The lesion involves the arm and leg. The patient indicates burning, pain and itching. The patient indicates the lesion is raised or bumpy. The patient considered this skin that appeared healthy to them. A close-up photograph. The condition has been present for less than one week.
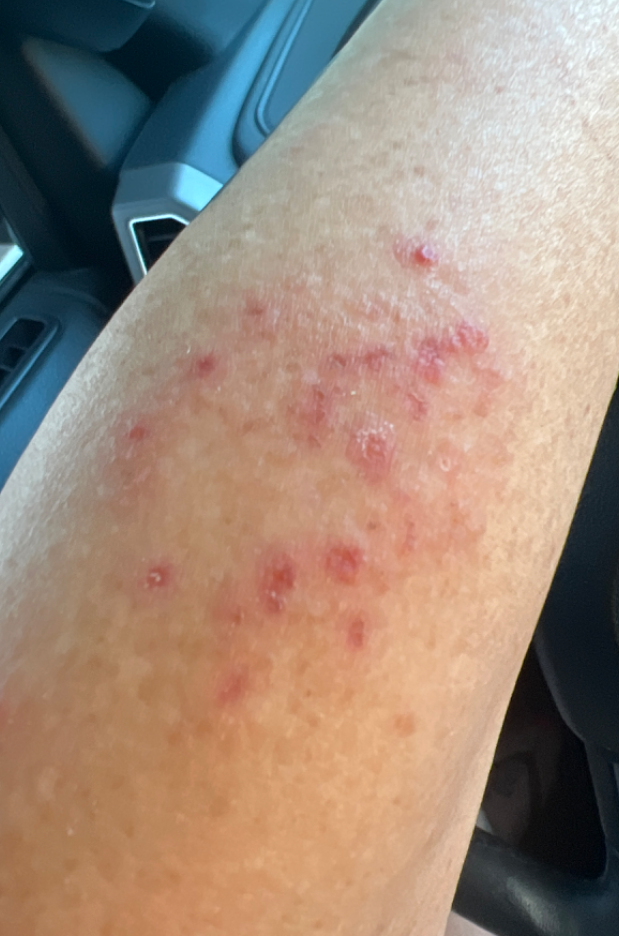Tinea, Insect Bite and Allergic Contact Dermatitis were each considered, in no particular order.